A skin lesion imaged with a dermatoscope.
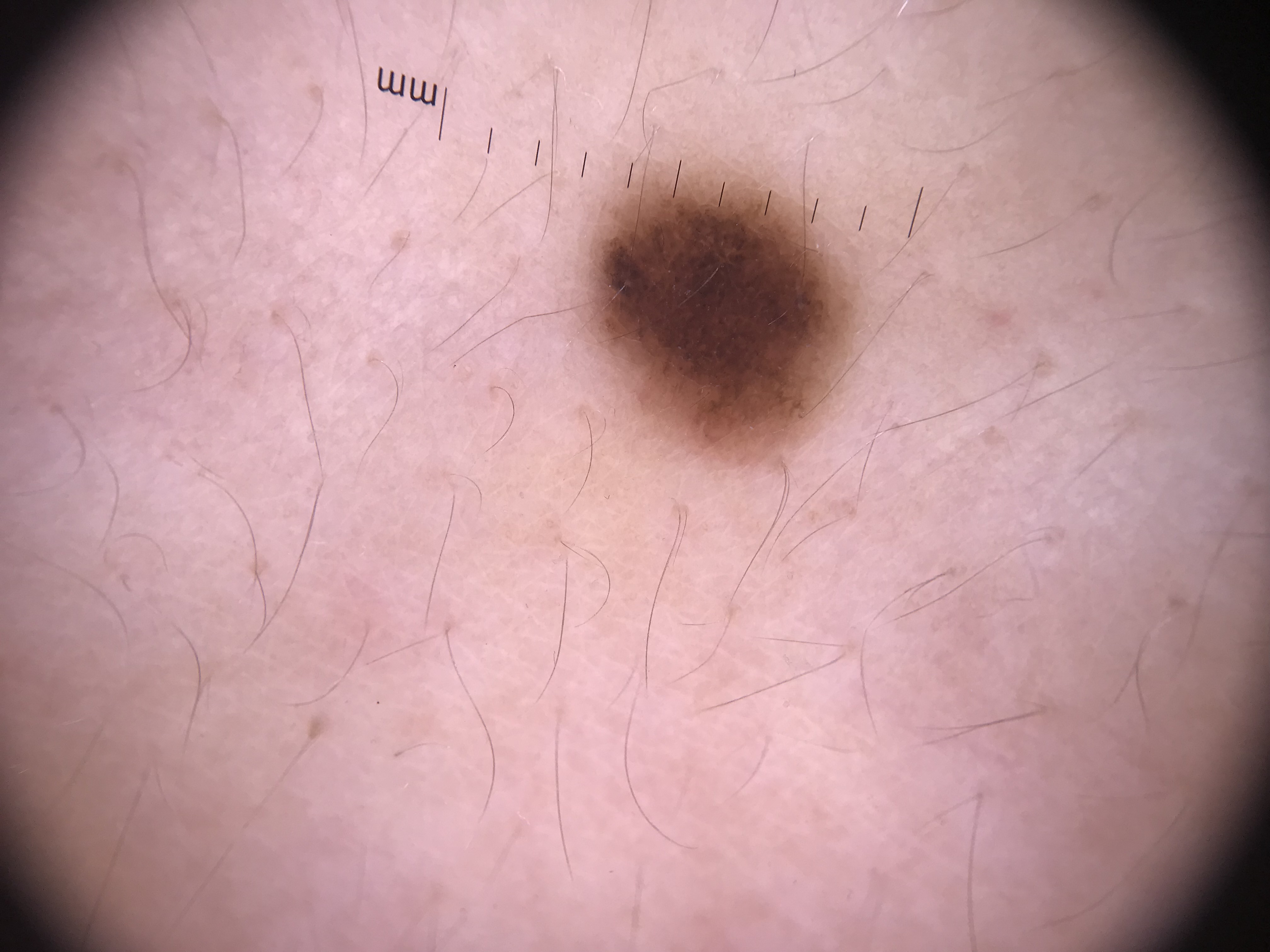Consistent with a dysplastic junctional nevus.